A dermoscopic photograph of a skin lesion.
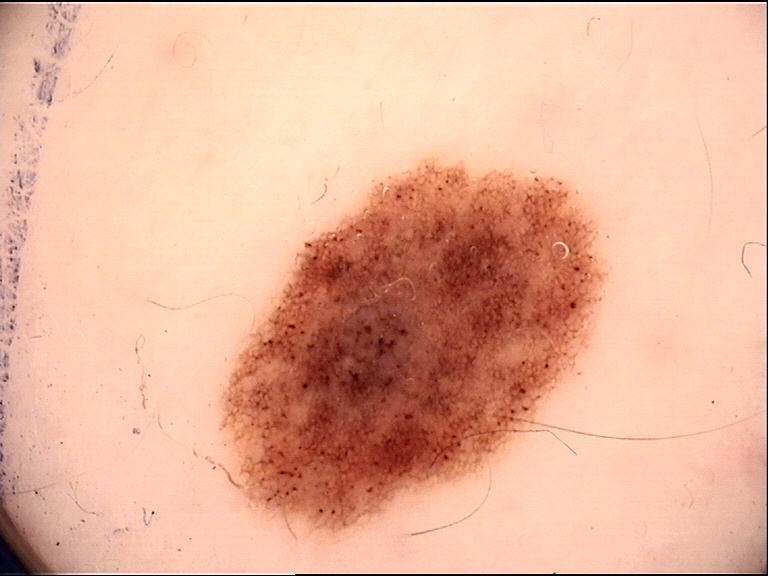The diagnosis was a benign lesion — a dysplastic compound nevus.